A clinical photograph showing a skin lesion. A patient in their 50s:
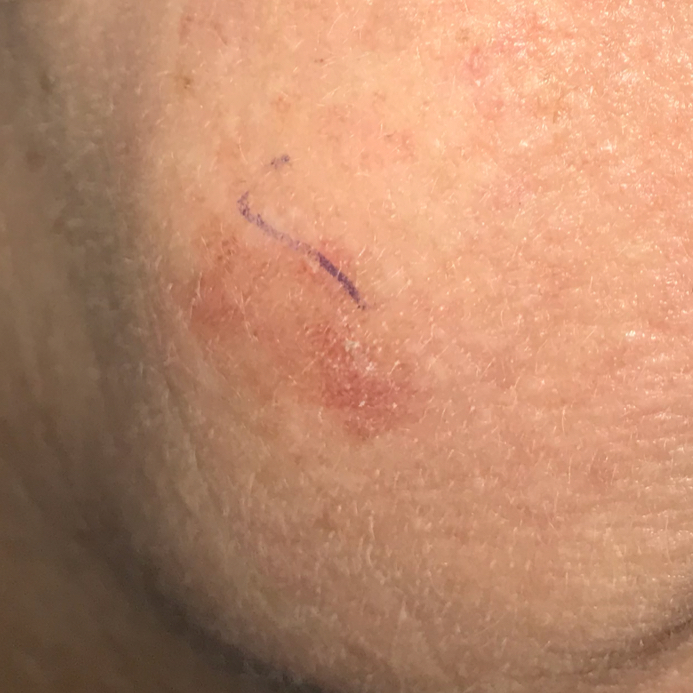| key | value |
|---|---|
| body site | the face |
| reported symptoms | growth, itching, change in appearance |
| assessment | actinic keratosis (clinical consensus) |